A patient aged 64. A clinical close-up photograph of a skin lesion.
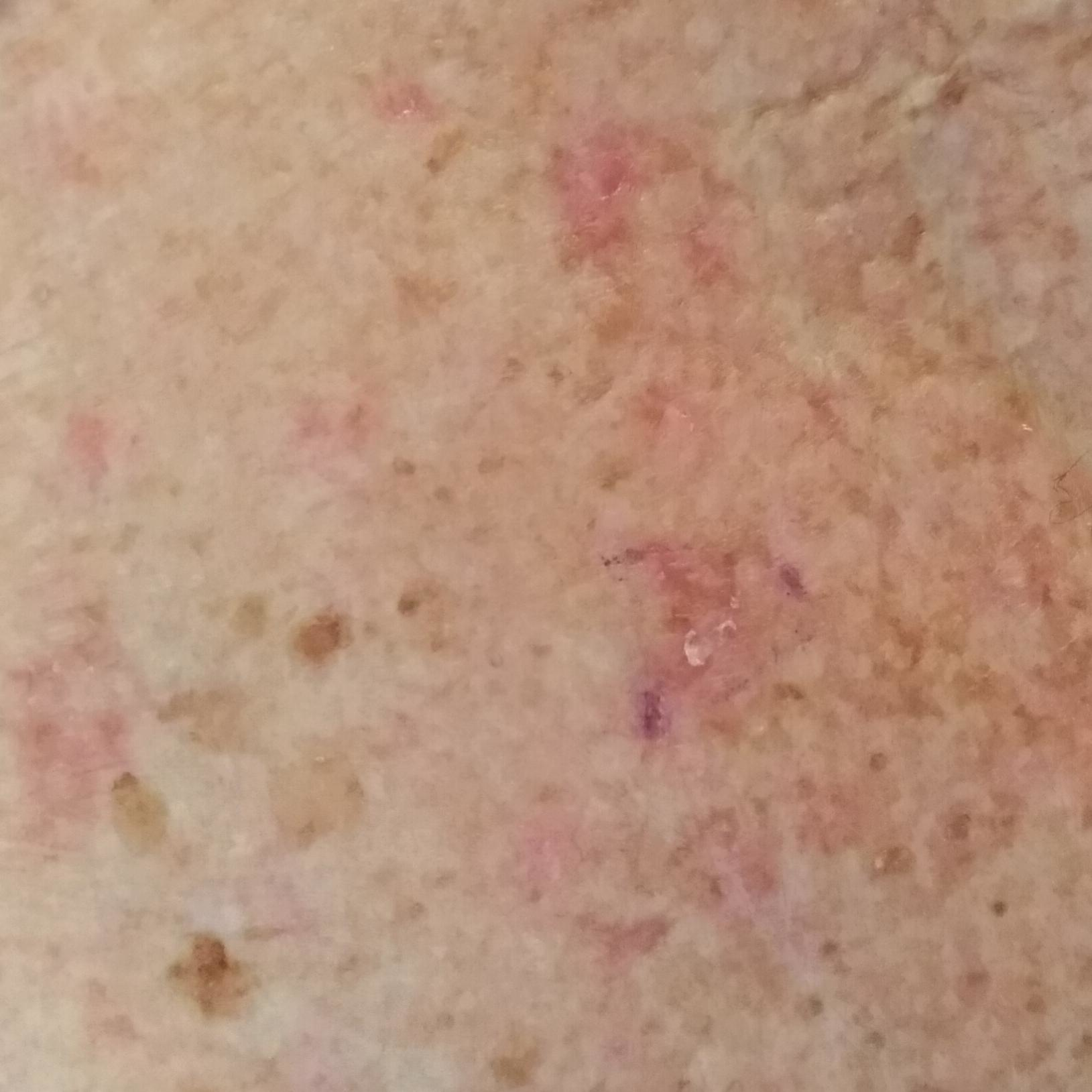Located on the neck.
The patient reports that the lesion itches.
Diagnosed by dermatologist consensus as an actinic keratosis.